This image was taken at an angle · no constitutional symptoms were reported · the affected area is the back of the hand and arm · the lesion is associated with itching and bothersome appearance · self-categorized by the patient as a rash · the lesion is described as fluid-filled and raised or bumpy · the patient is 40–49, male · skin tone: Fitzpatrick I; lay reviewers estimated Monk skin tone scale 2 or 3 (two reviewer pools) · reported duration is one to four weeks — 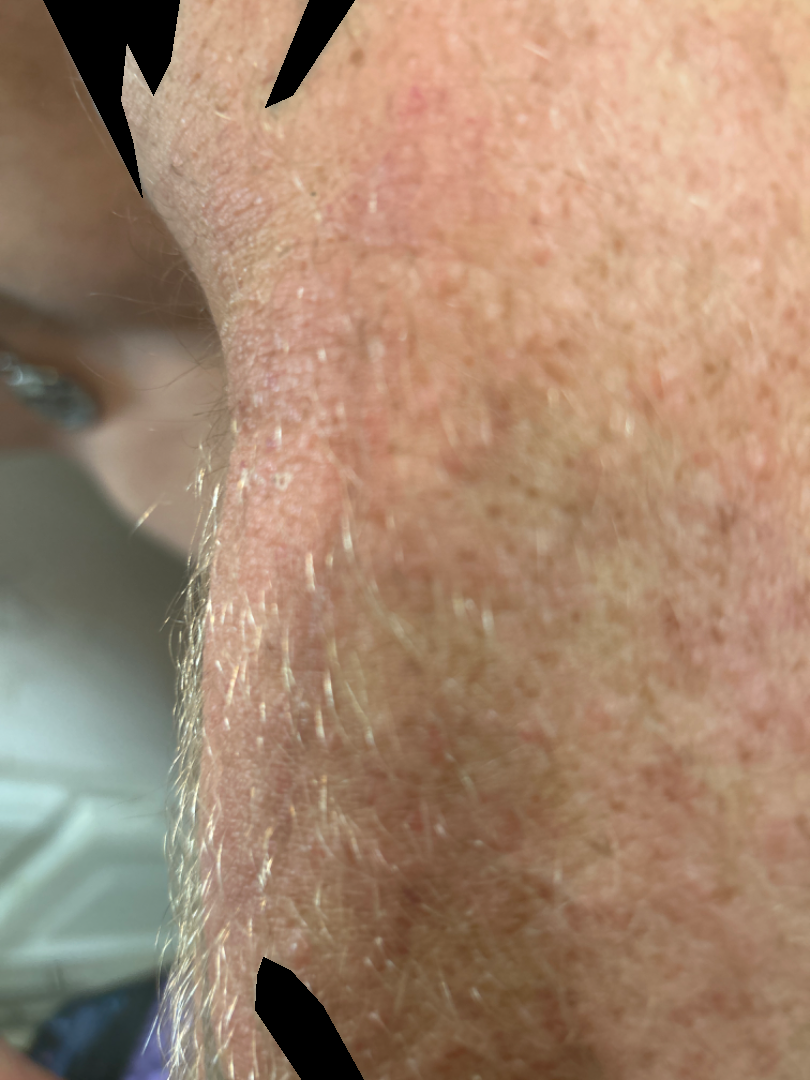<case>
<differential>
  <tied_lead>Psoriasis, Eczema</tied_lead>
</differential>
</case>